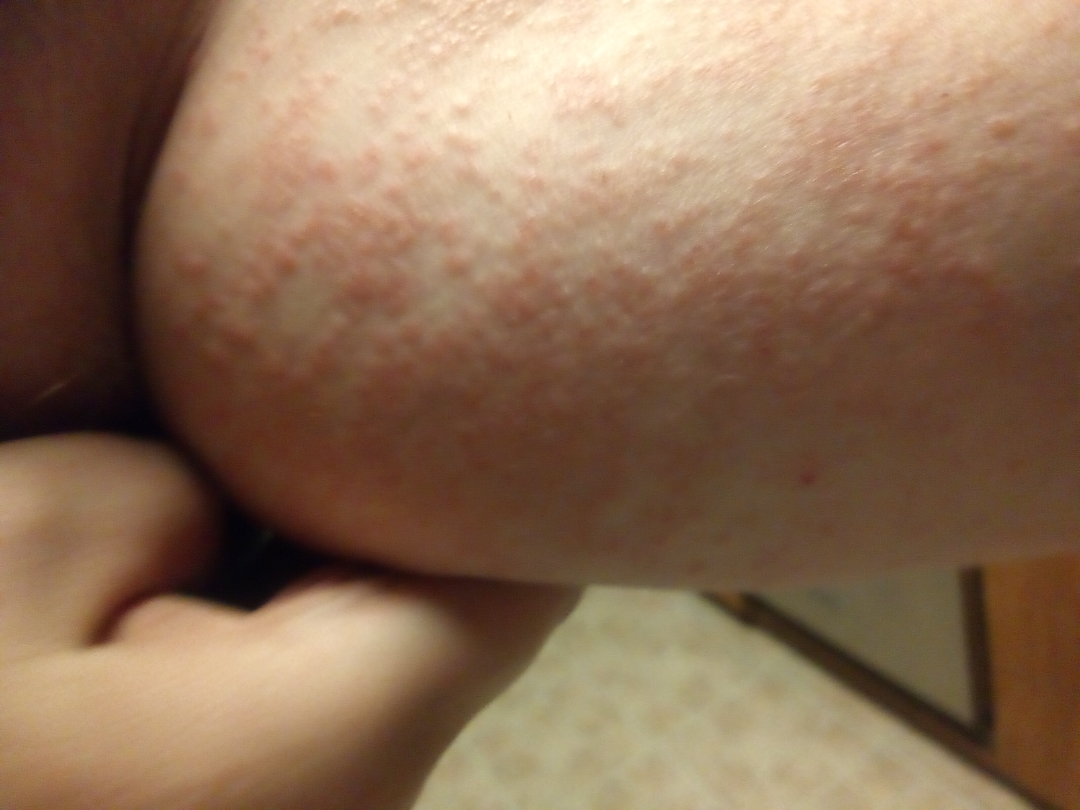The case was difficult to assess from the available photograph.
The photograph is a close-up of the affected area.
Human graders estimated 3 on the Monk Skin Tone.
The patient reports the lesion is raised or bumpy.